A dermoscopic close-up of a skin lesion.
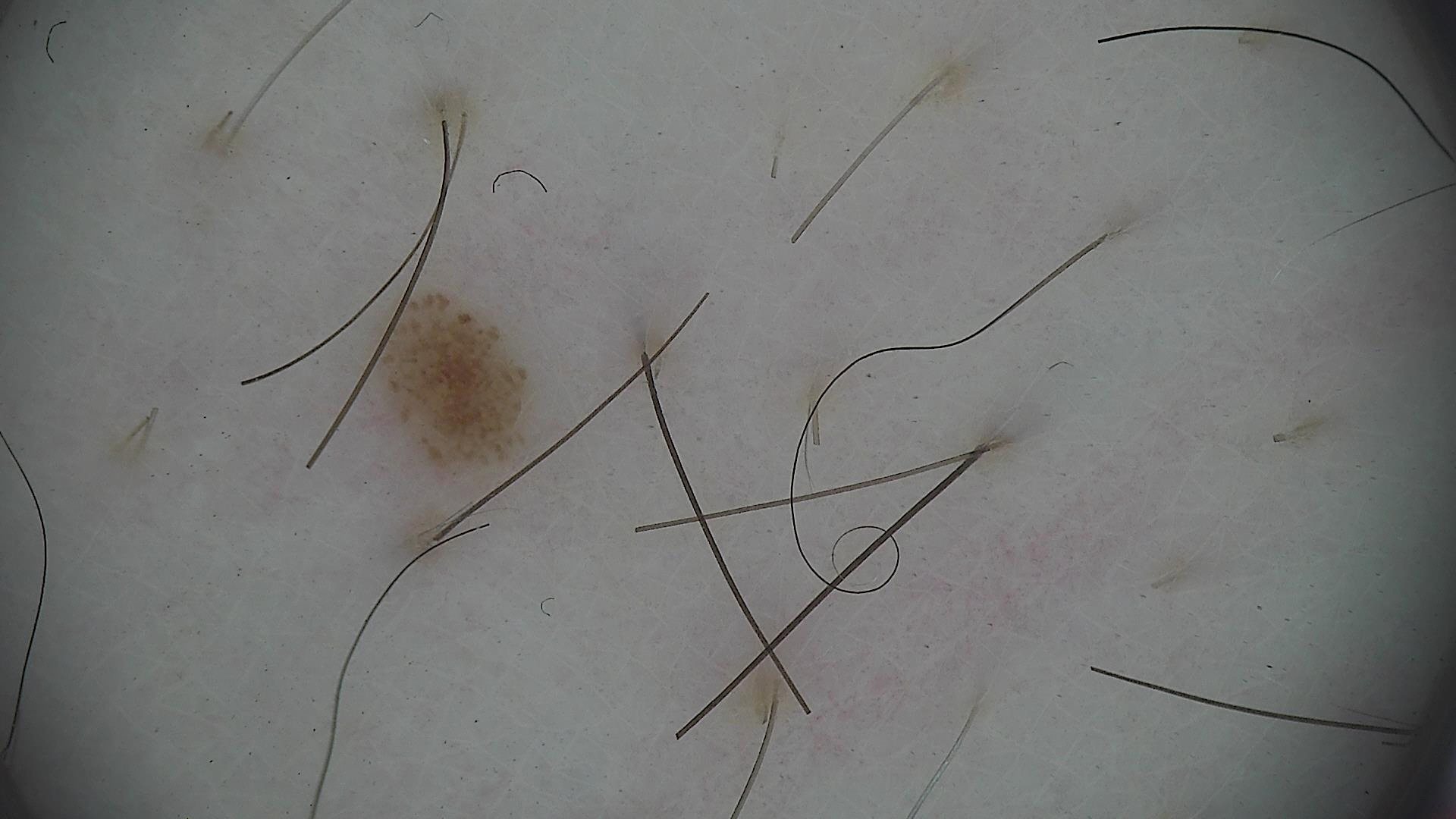| feature | finding |
|---|---|
| class | dysplastic junctional nevus (expert consensus) |